A male subject in their mid-40s; per the chart, a previous melanoma but no melanoma in first-degree relatives; a dermoscopic photograph of a skin lesion; the patient is Fitzpatrick II:
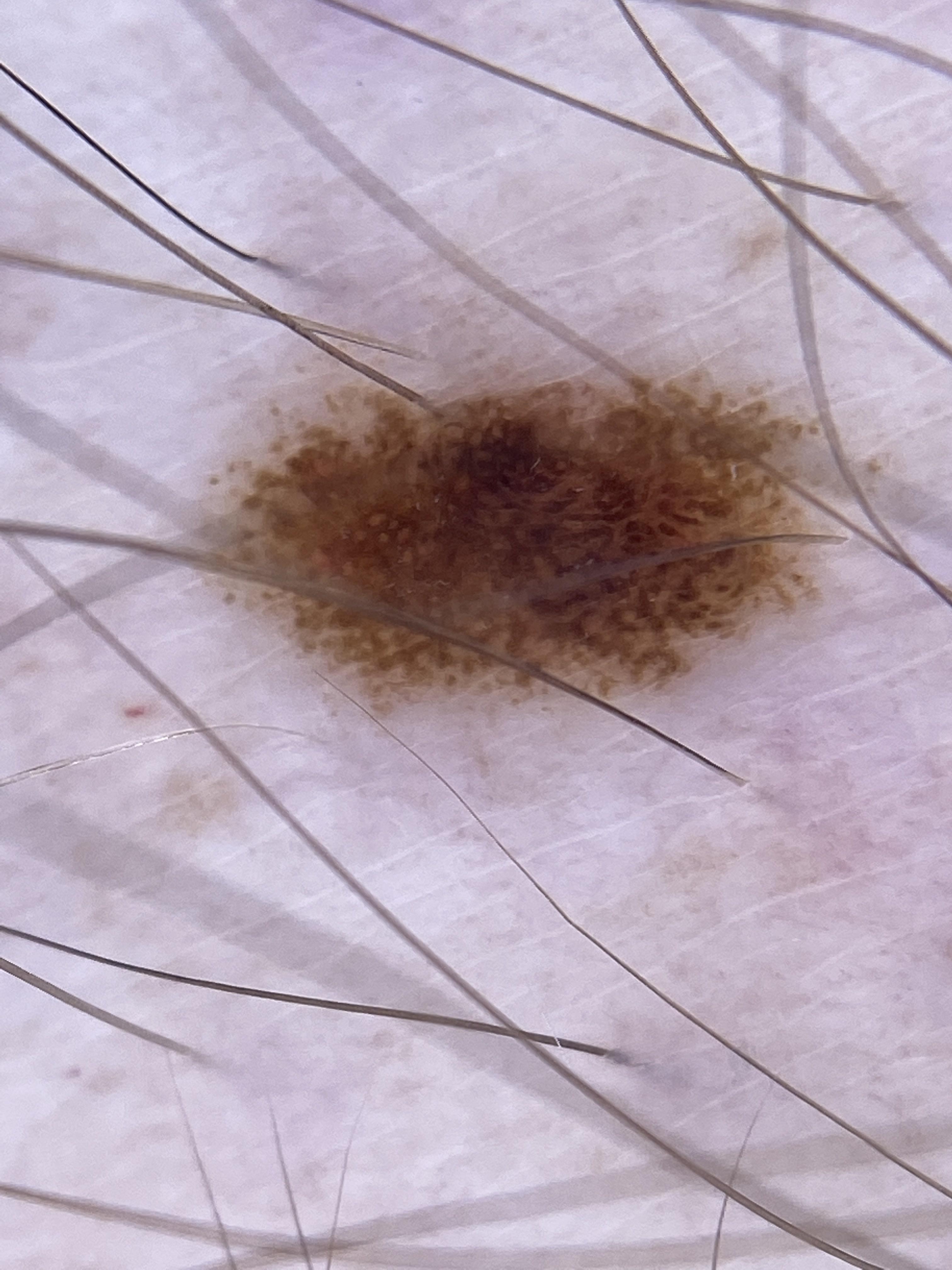Q: What is the anatomic site?
A: a lower extremity
Q: What was the clinical impression?
A: Nevus